A dermatoscopic image of a skin lesion — 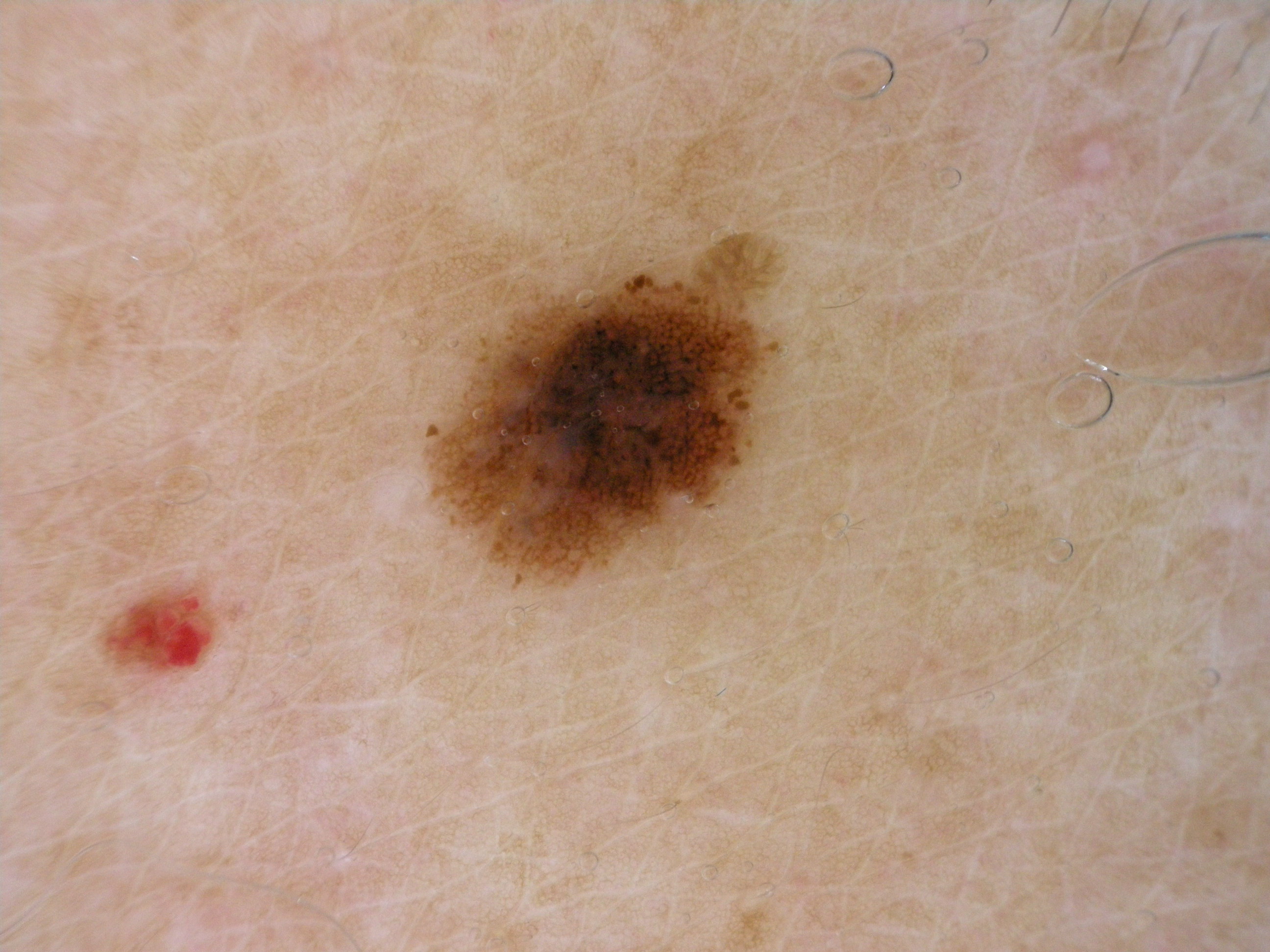Findings:
- lesion bbox: bbox(425, 232, 783, 585)
- dermoscopic pattern: globules and pigment network
- assessment: a melanocytic nevus, a benign skin lesion